The patient is a male aged 53 to 57 · a dermoscopic image of a skin lesion:
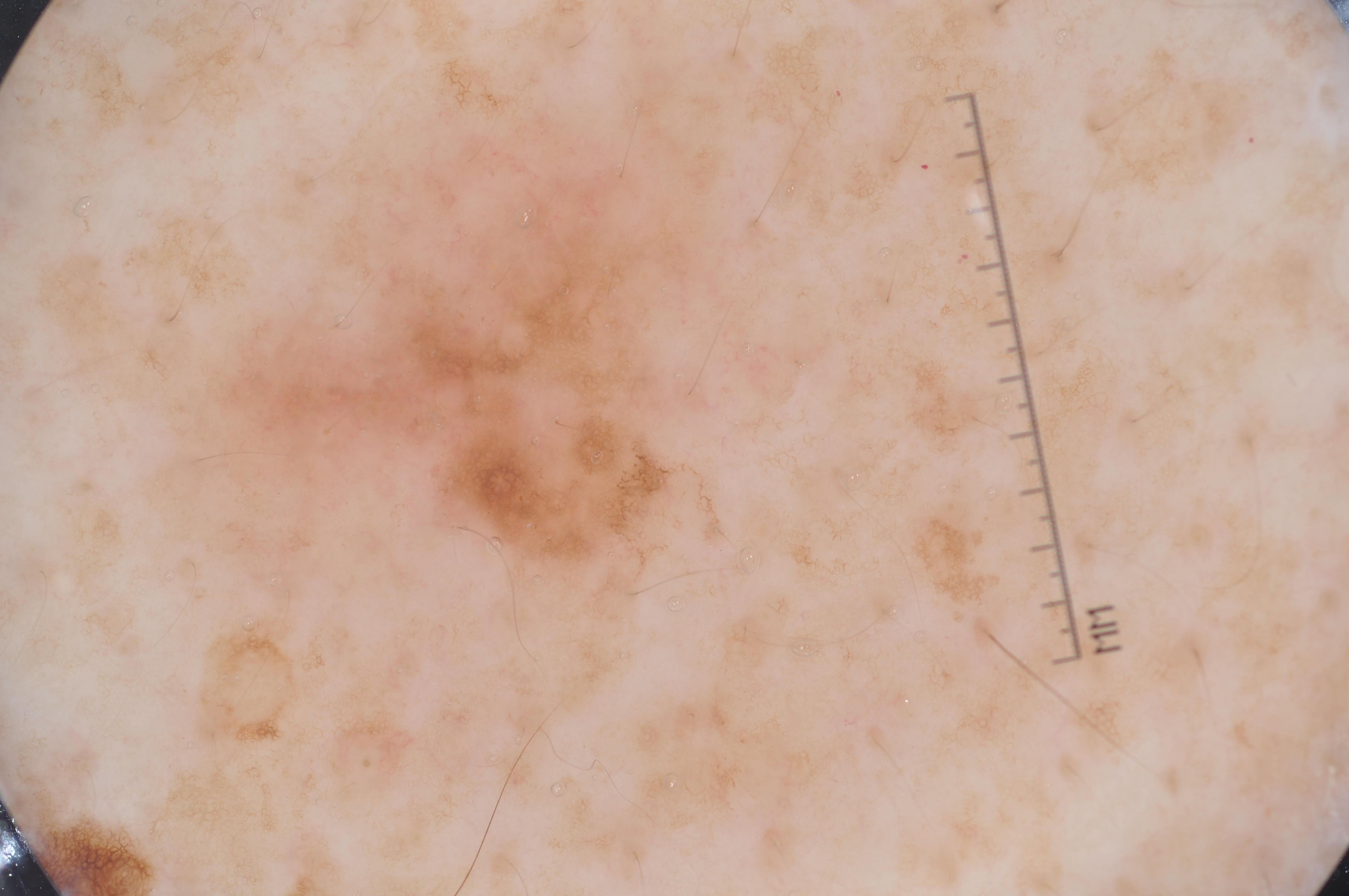Case summary:
In (x1, y1, x2, y2) order, the lesion's extent is [211, 168, 695, 574]. Dermoscopy demonstrates pigment network. A mid-sized lesion within the field.
Pathology:
On biopsy, the diagnosis was a melanoma, a malignant skin lesion.